The patient reports the condition has been present for less than one week · located on the leg · the patient reports the lesion is rough or flaky and flat · the patient considered this a rash · associated systemic symptoms include joint pain · the contributor is 30–39, male · a close-up photograph · the patient reports bothersome appearance and pain · skin tone: FST II:
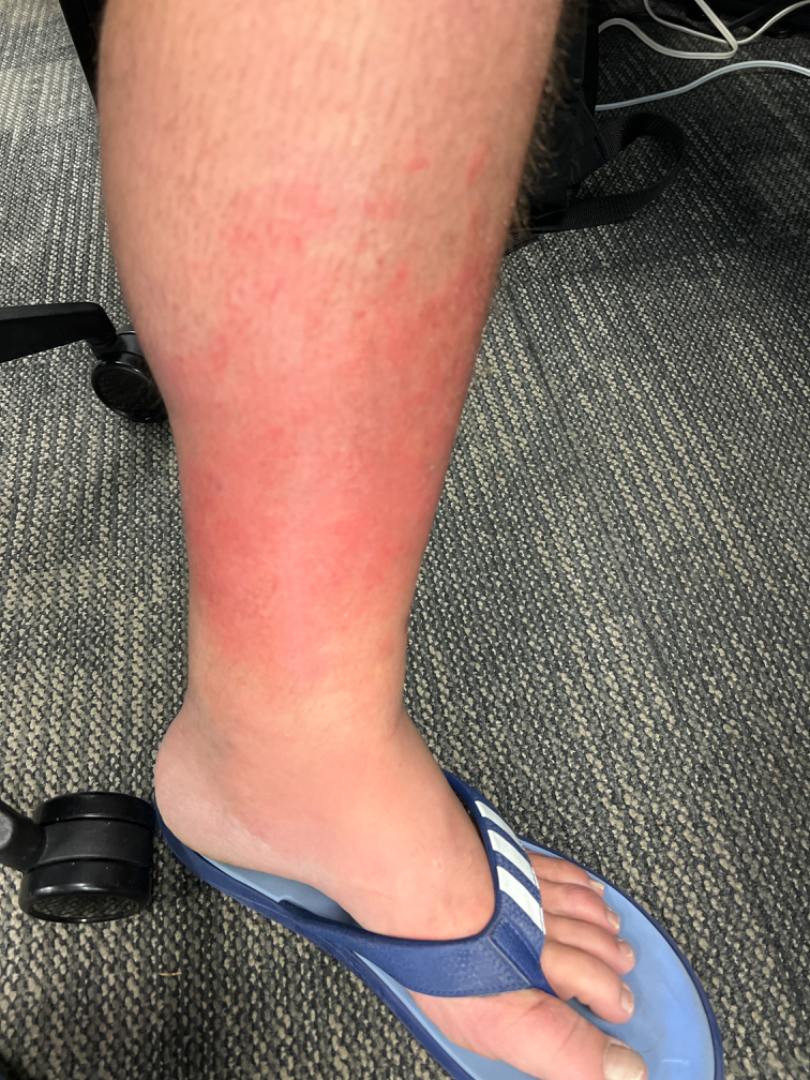Assessment: The reviewing clinician's impression was: most consistent with Stasis Dermatitis.